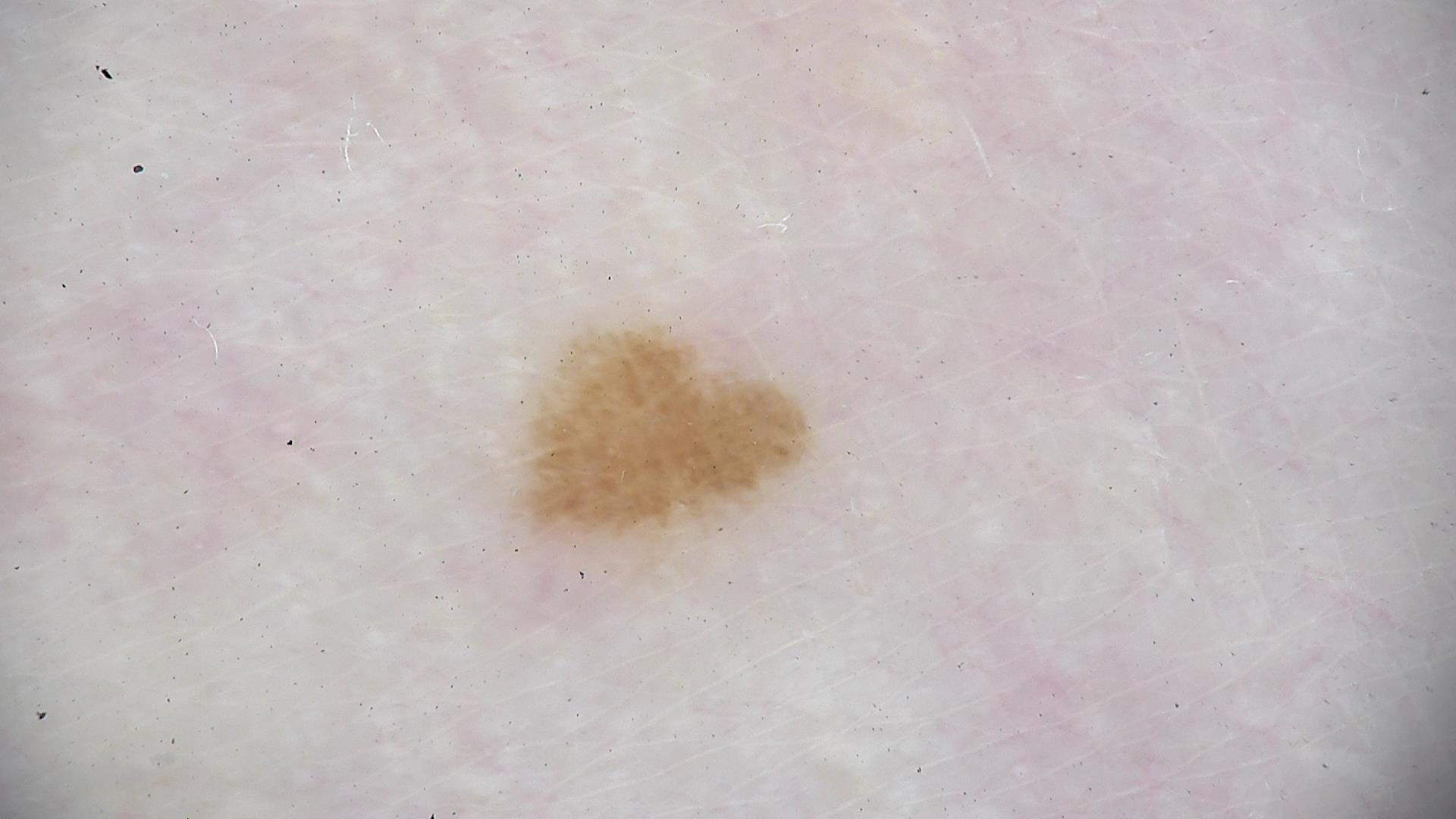Impression:
Consistent with an acral dysplastic junctional nevus.